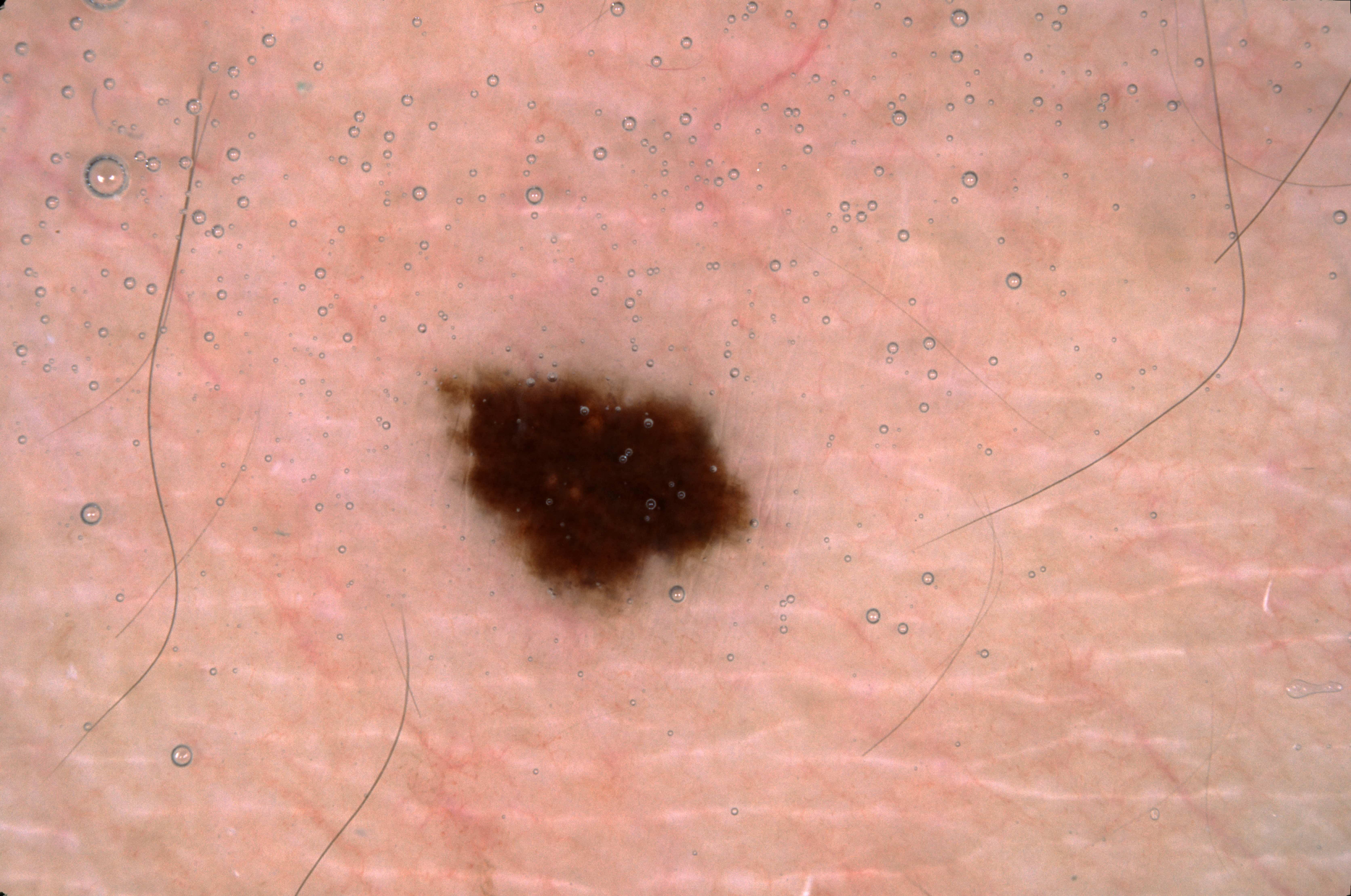Findings:
The subject is a male aged around 35. A dermoscopic view of a skin lesion. Dermoscopic assessment notes no pigment network, streaks, milia-like cysts, or negative network. As (left, top, right, bottom), the lesion occupies the region <bbox>435, 363, 754, 618</bbox>.
Impression:
Expert review diagnosed this as a melanocytic nevus.